A dermatoscopic image of a skin lesion: 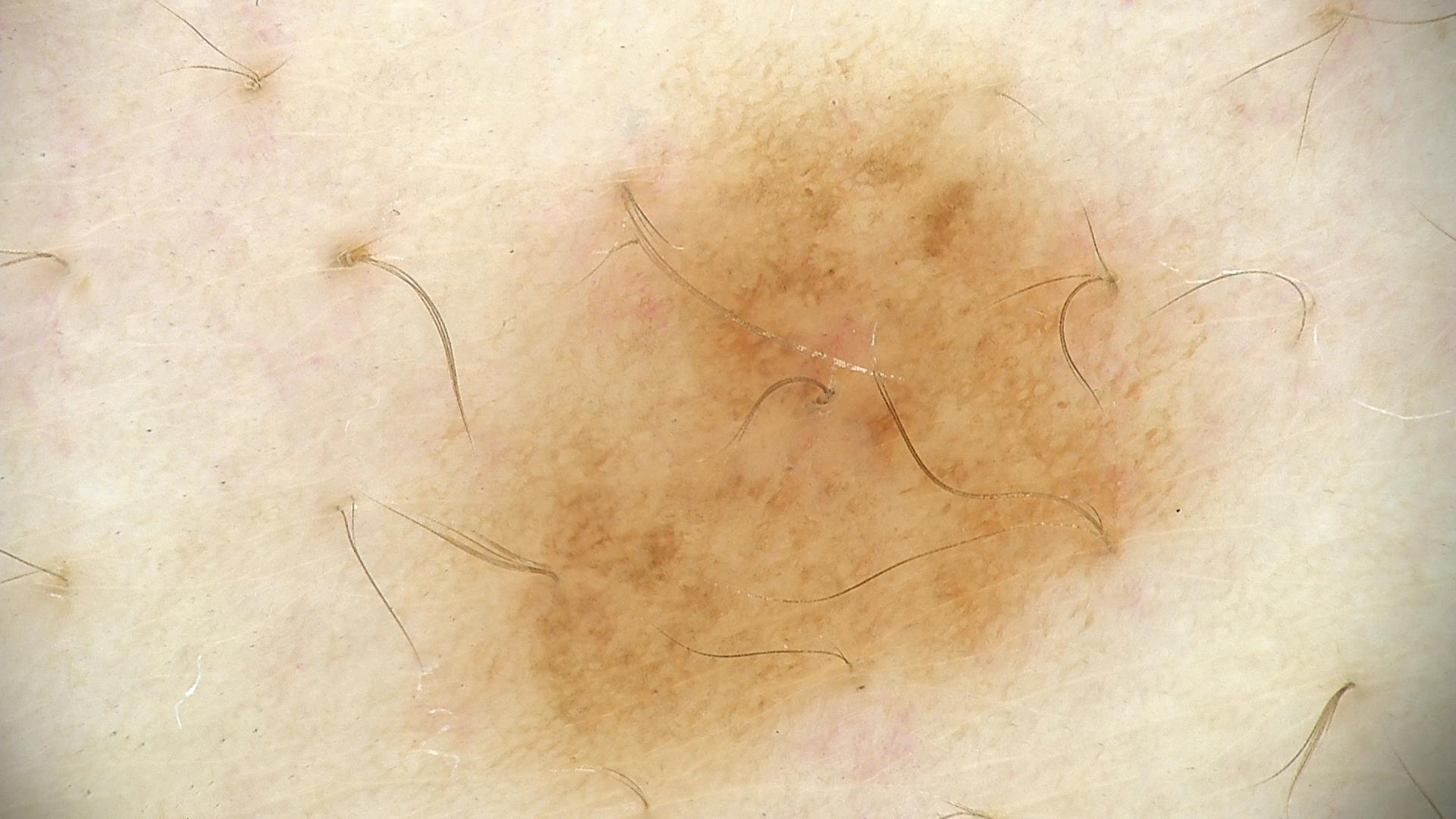<lesion>
<diagnosis>
<name>dysplastic junctional nevus</name>
<code>jd</code>
<malignancy>benign</malignancy>
<super_class>melanocytic</super_class>
<confirmation>expert consensus</confirmation>
</diagnosis>
</lesion>